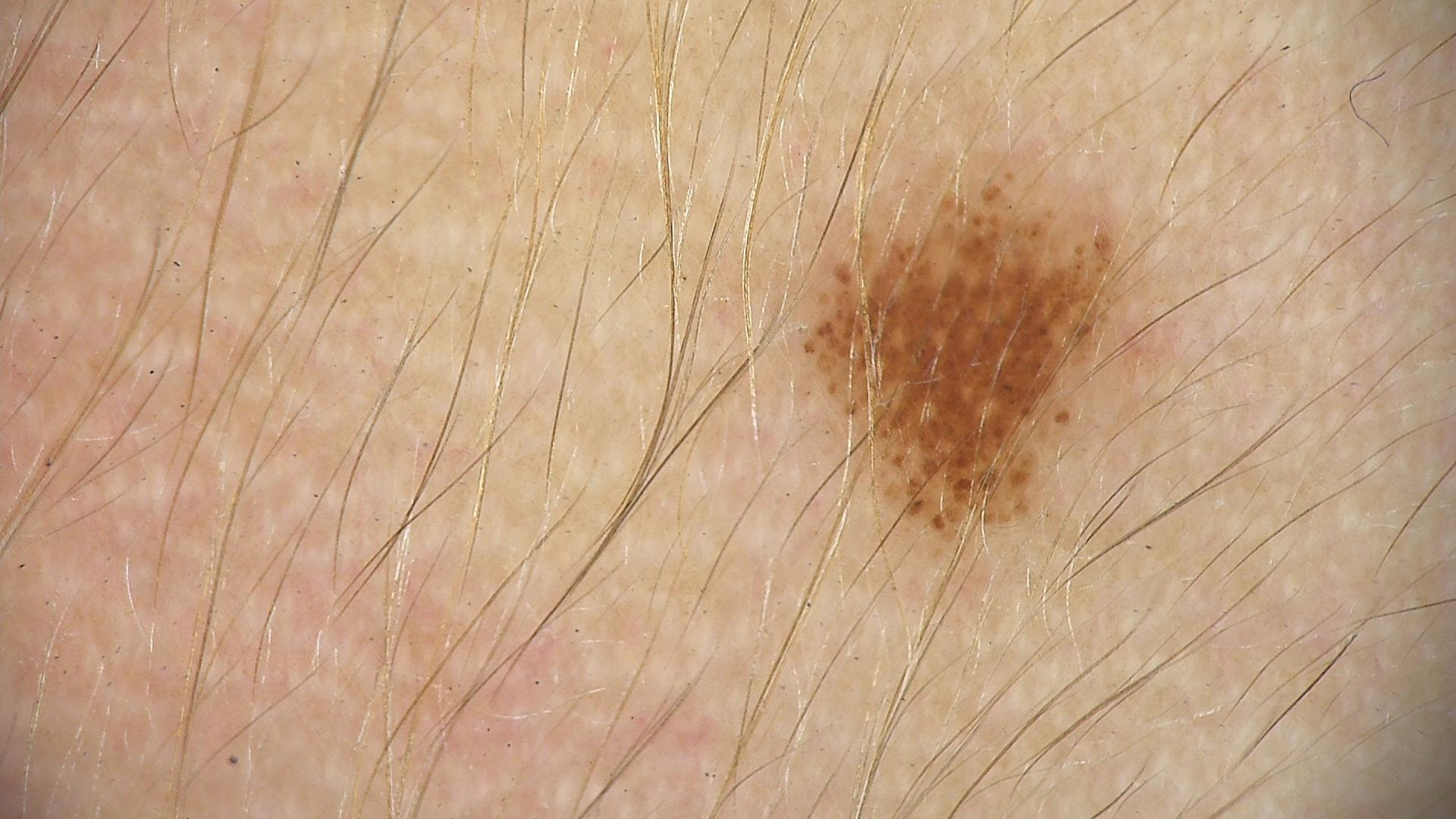A dermatoscopic image of a skin lesion. Diagnosed as a benign lesion — a dysplastic junctional nevus.